A dermatoscopic image of a skin lesion: 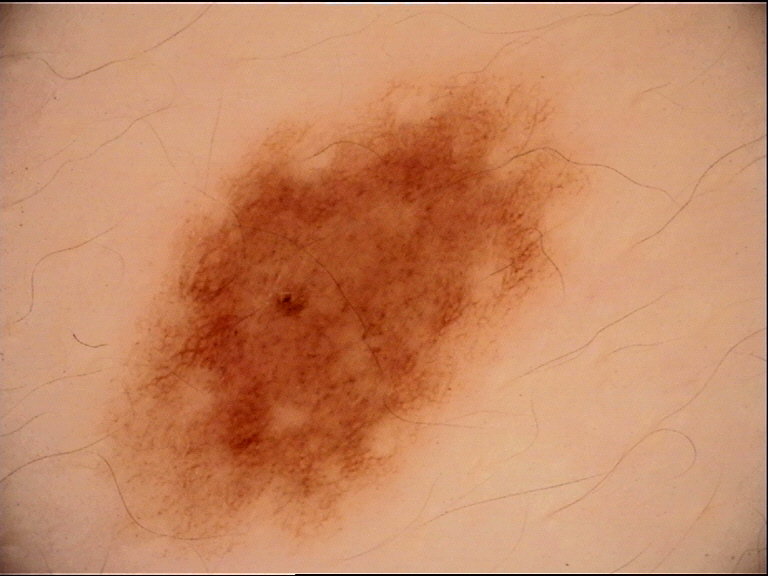Diagnosed as a dysplastic junctional nevus.